A skin lesion imaged with a dermatoscope: 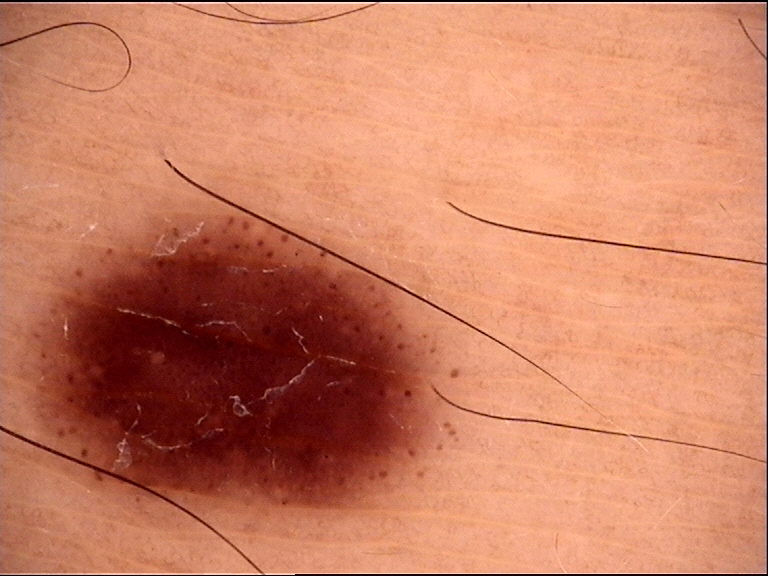The diagnosis was a benign lesion — a dysplastic junctional nevus.